Recorded as FST II. A clinical photograph of a skin lesion. A female patient aged 38 to 42.
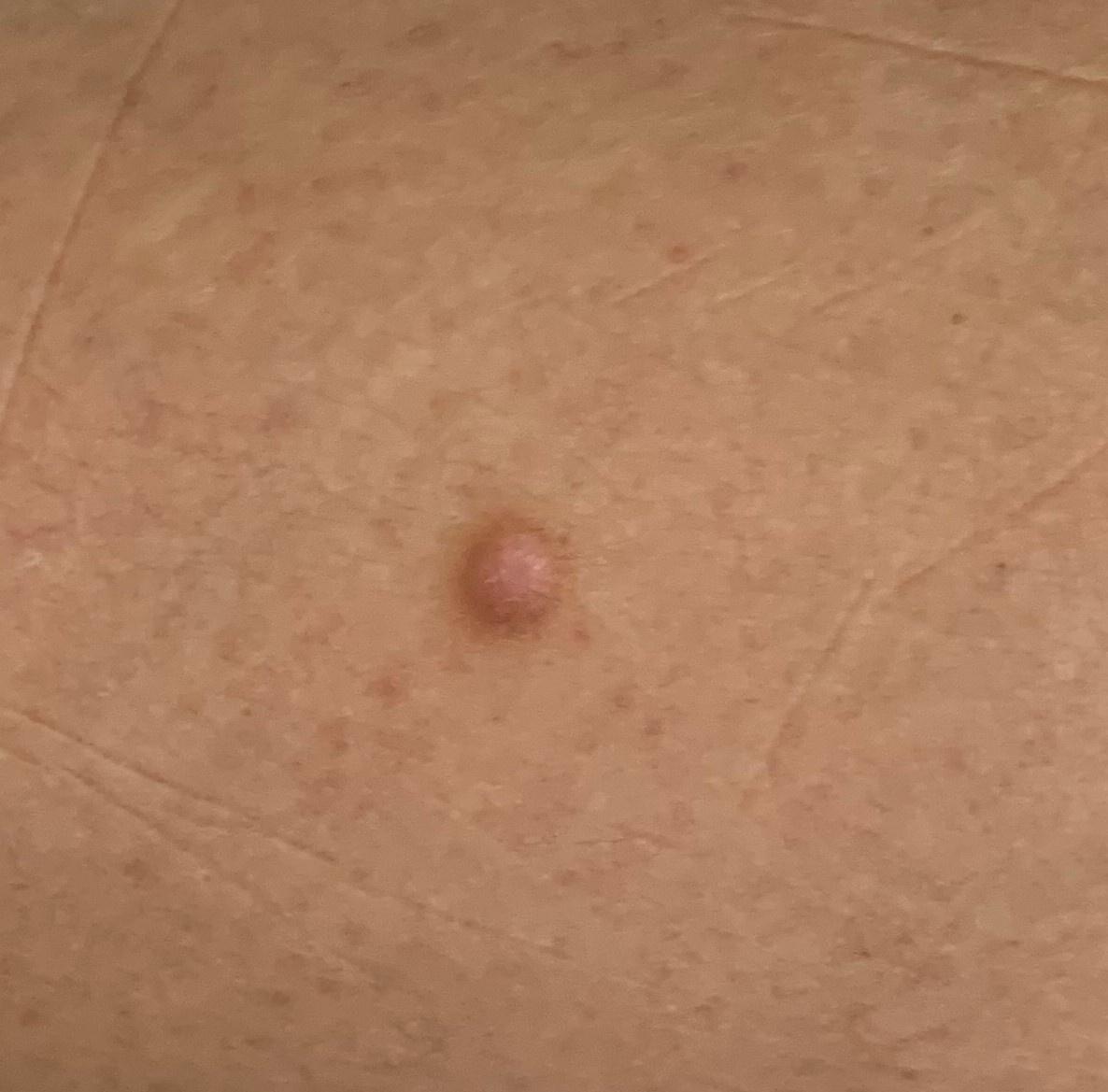Case:
– site · a lower extremity
– diagnostic label · Dermatofibroma (biopsy-proven)